A dermoscopic image of a skin lesion. A male patient, aged 23 to 27:
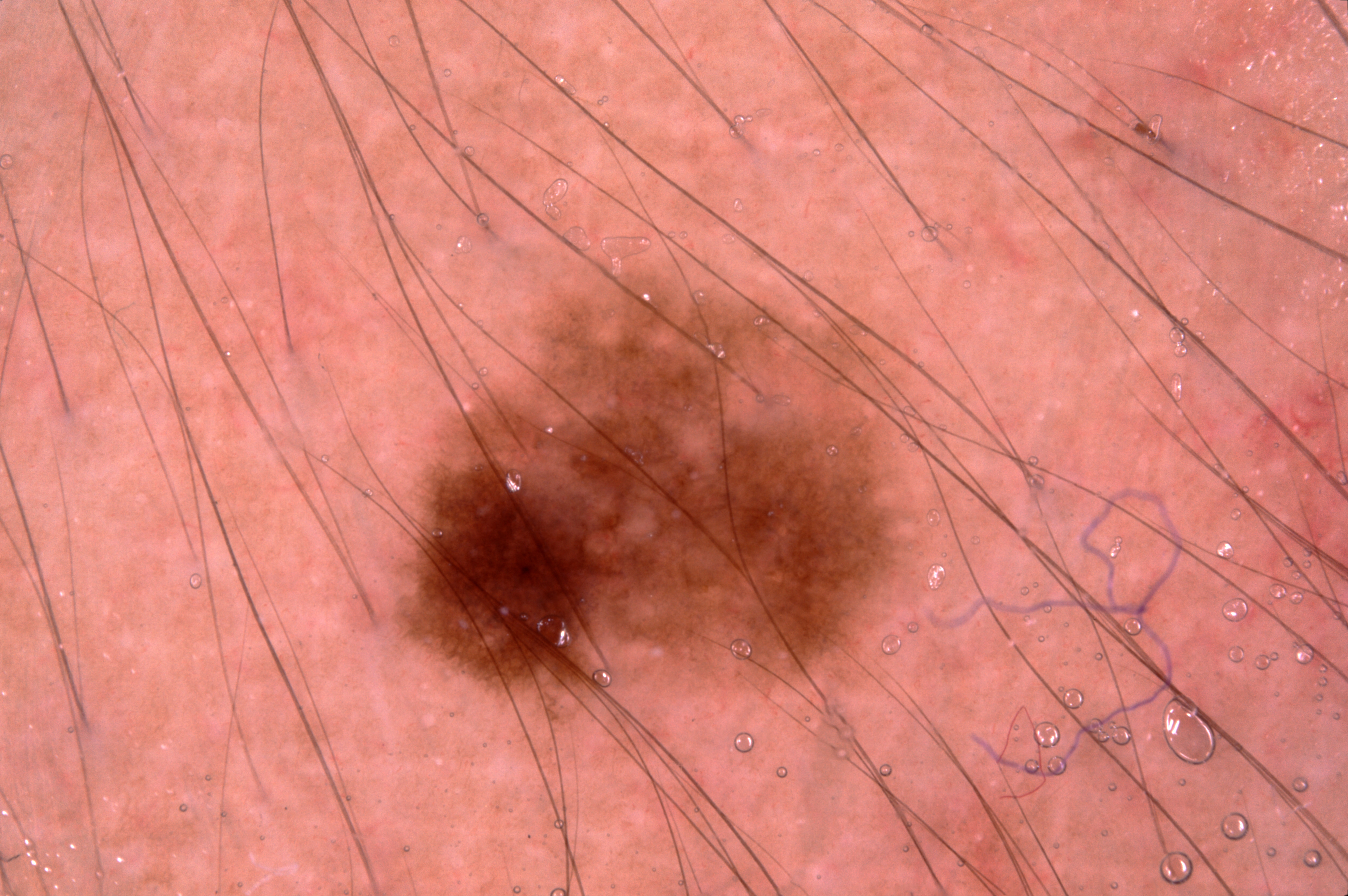{"lesion_location": {"bbox_xyxy": [374, 241, 929, 742]}, "dermoscopic_features": {"present": ["pigment network"], "absent": ["milia-like cysts", "streaks", "negative network"]}, "diagnosis": {"name": "melanocytic nevus", "malignancy": "benign", "lineage": "melanocytic", "provenance": "clinical"}}